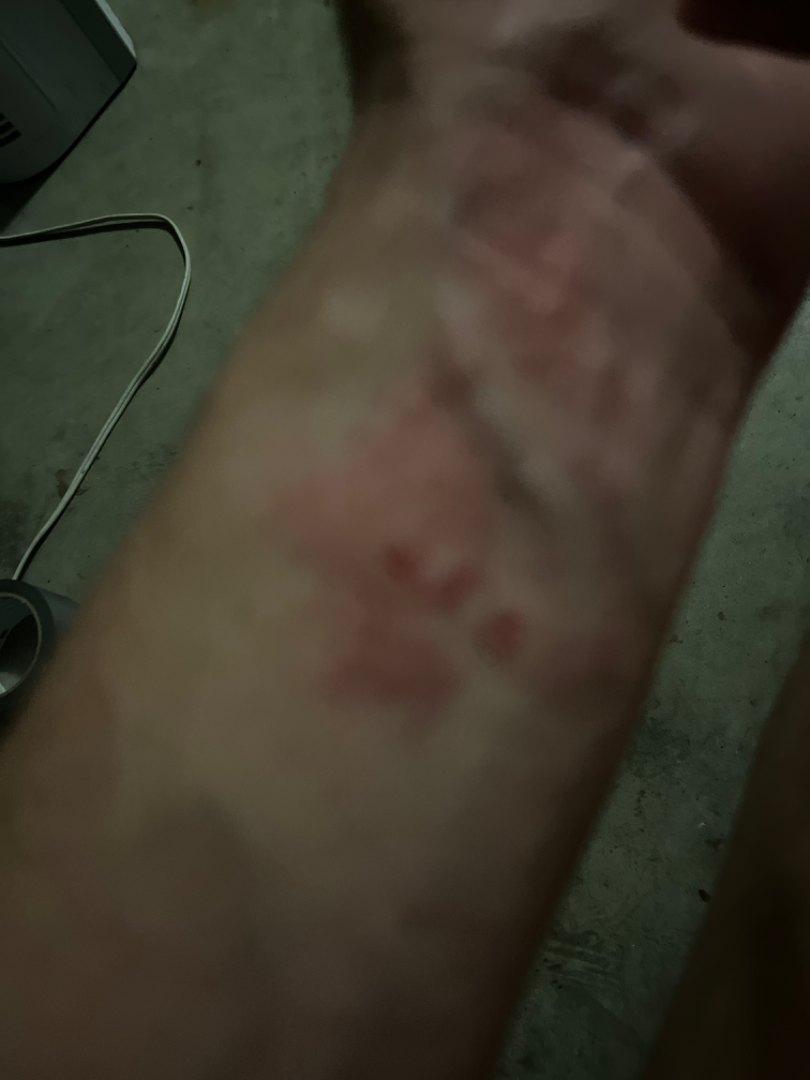The image was not sufficient for the reviewer to characterize the skin condition. The photograph is a close-up of the affected area. The affected area is the arm.